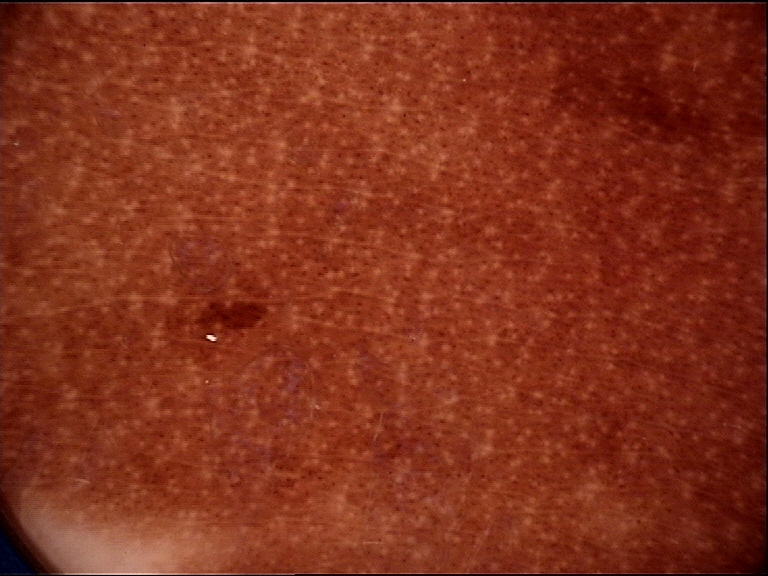Findings: A dermoscopic photograph of a skin lesion. This is a banal lesion. Impression: Diagnosed as a congenital compound nevus.